The affected area is the front of the torso. This image was taken at a distance. The subject is female — 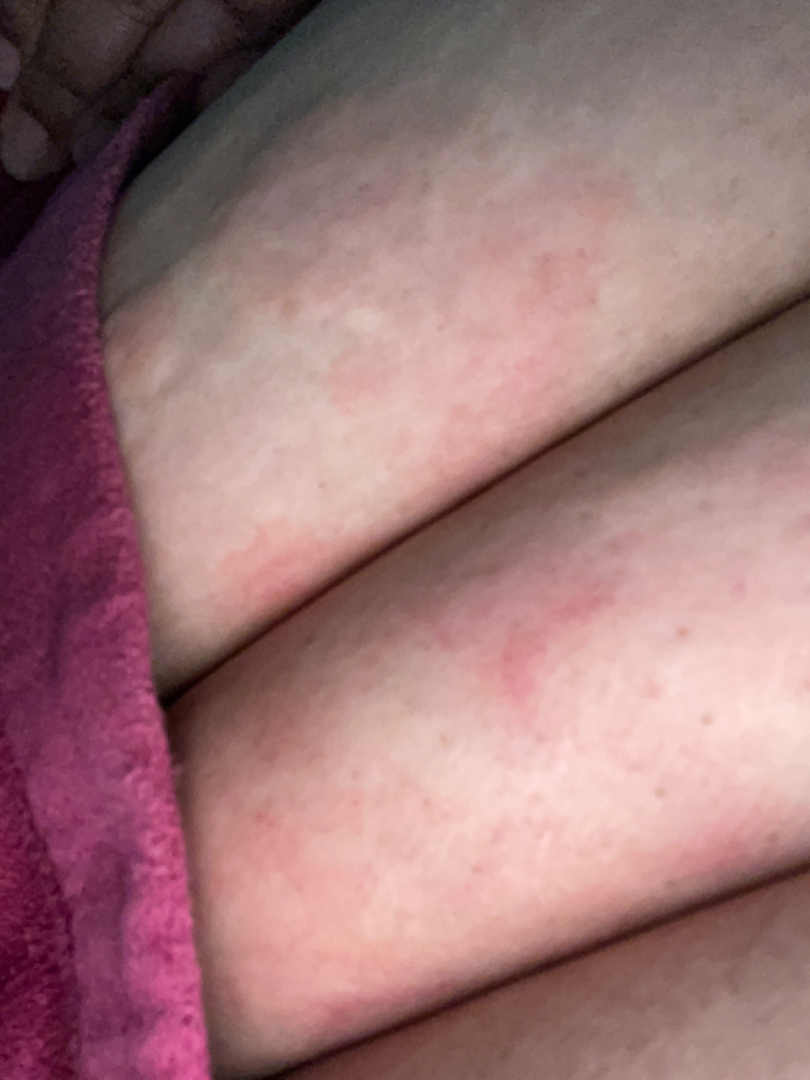{"assessment": "indeterminate from the photograph"}